The patient was assessed as Fitzpatrick skin type III · a male subject aged approximately 55 · per the chart, melanoma in a first-degree relative · contact-polarized dermoscopy of a skin lesion: 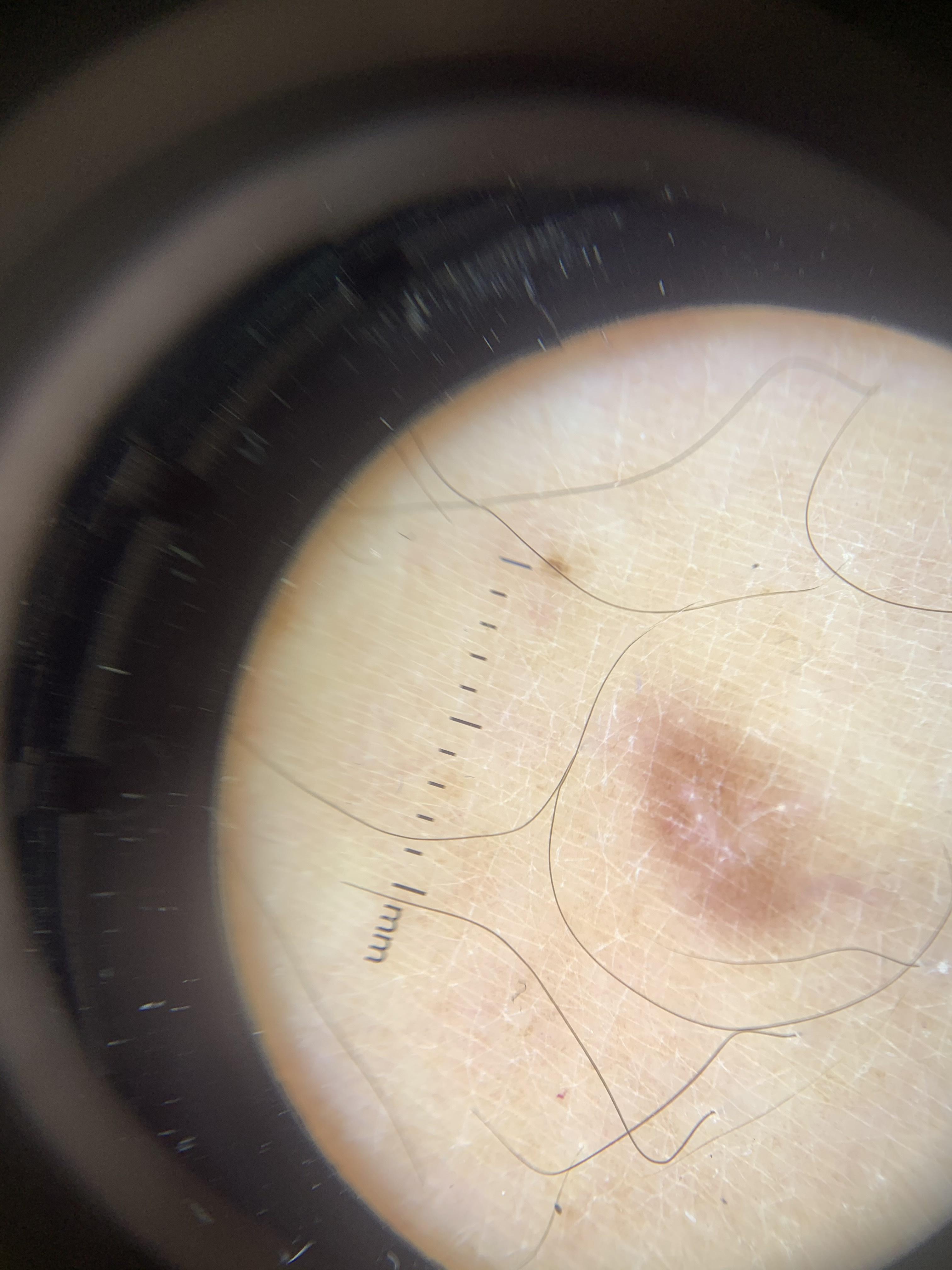Findings:
The lesion is on a lower extremity.
Impression:
Clinically diagnosed as a dermatofibroma.